A dermoscopic image of a skin lesion.
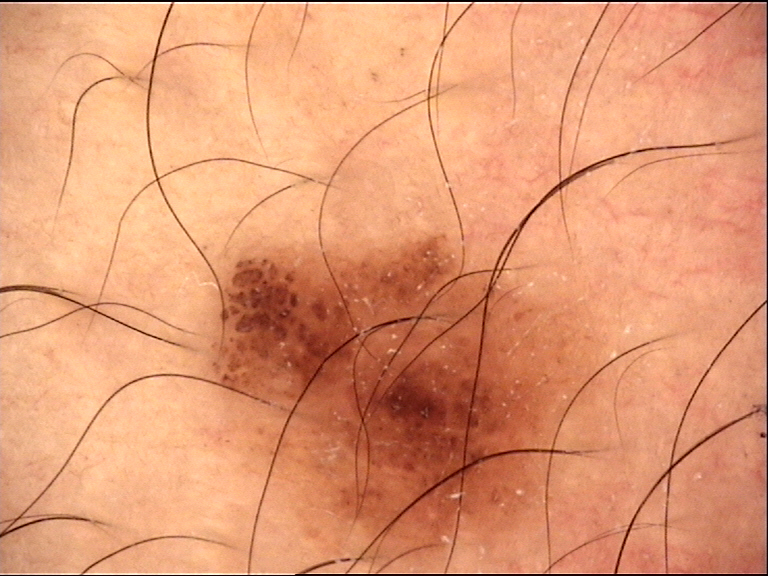subtype: banal
label: compound nevus (expert consensus)